A dermoscopic photograph of a skin lesion.
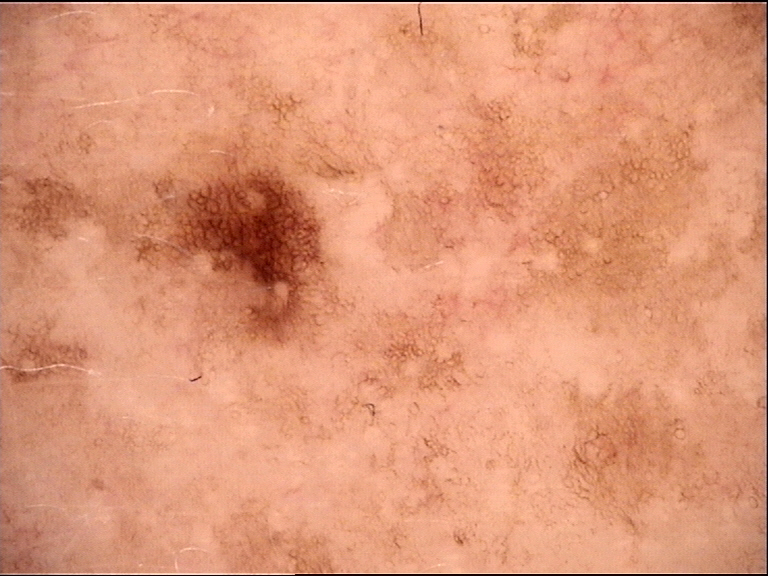The diagnosis was a dysplastic junctional nevus.